Texture is reported as raised or bumpy. Female contributor, age 18–29. The lesion is associated with itching. Reported duration is one to four weeks. This is a close-up image — 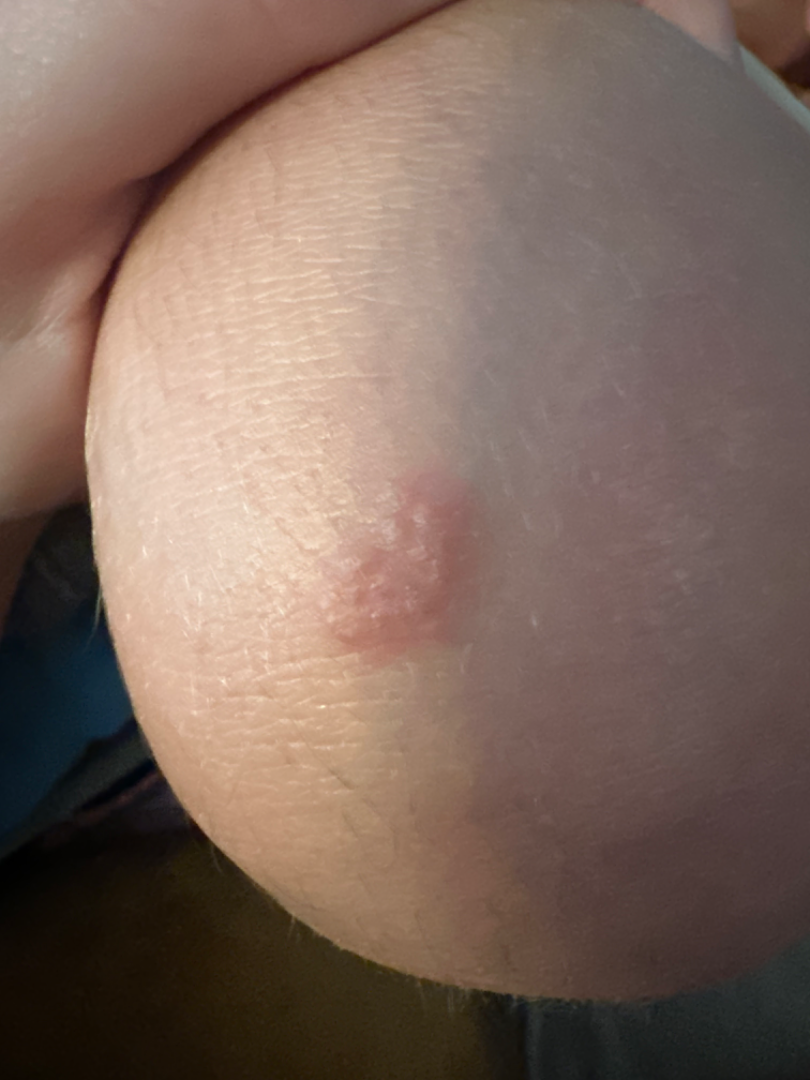Case summary:
– assessment — indeterminate